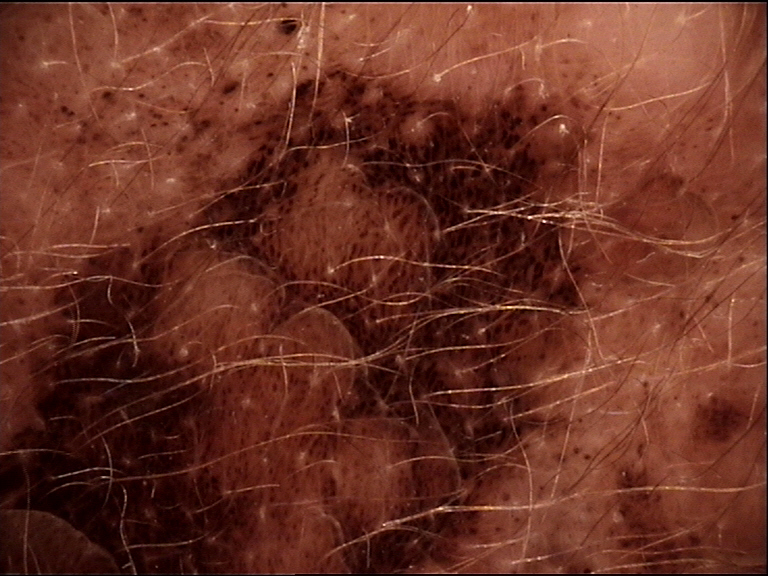Summary:
A dermoscopic image of a skin lesion. The morphology is that of a banal lesion.
Impression:
Labeled as a congenital compound nevus.